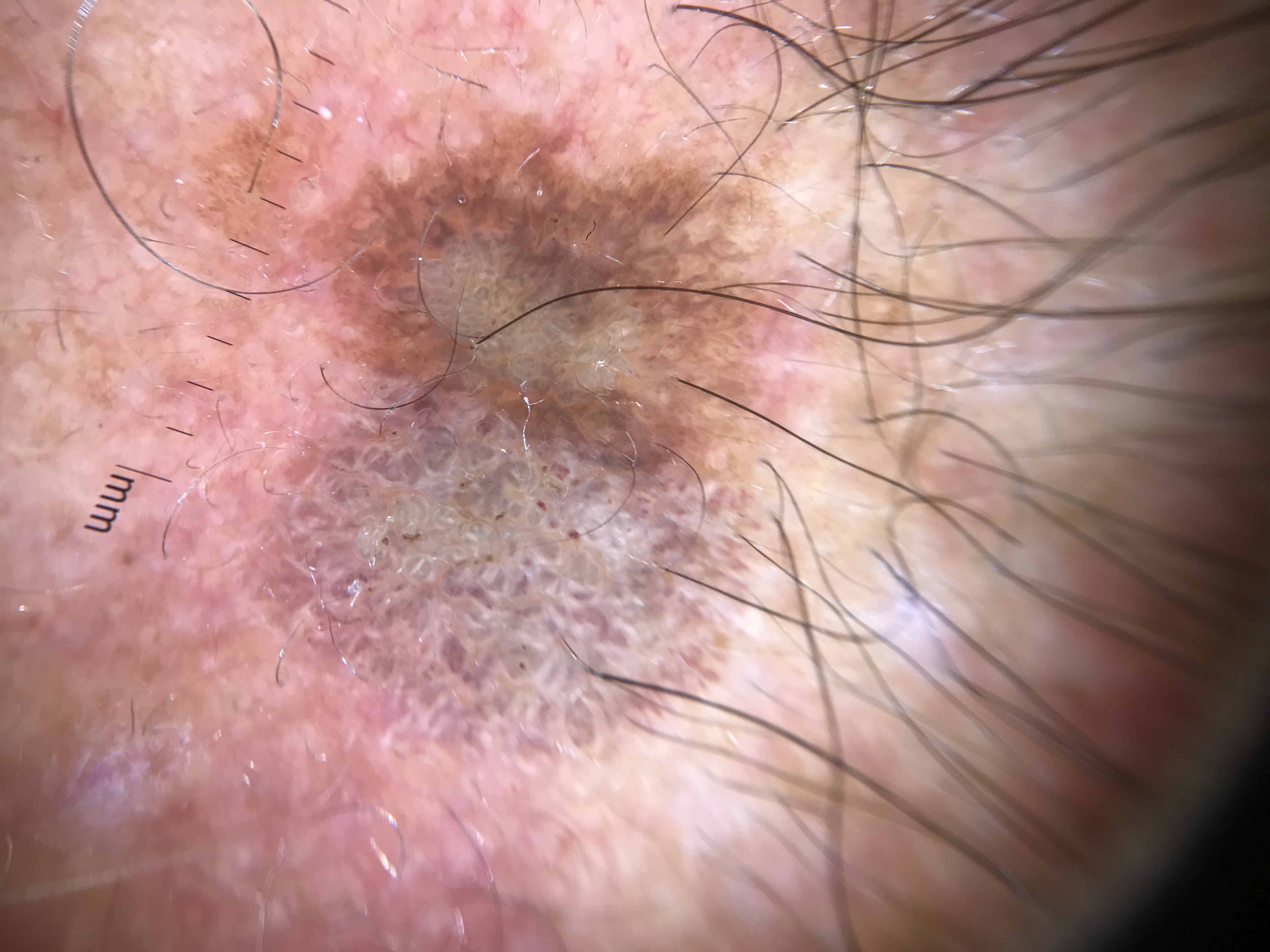Q: What is the imaging modality?
A: dermoscopy
Q: What is this lesion?
A: seborrheic keratosis (expert consensus)